A male patient 72 years old. The chart records prior skin cancer (patient or family) and no pesticide exposure. A clinical photograph showing a skin lesion. The patient was assessed as Fitzpatrick III — 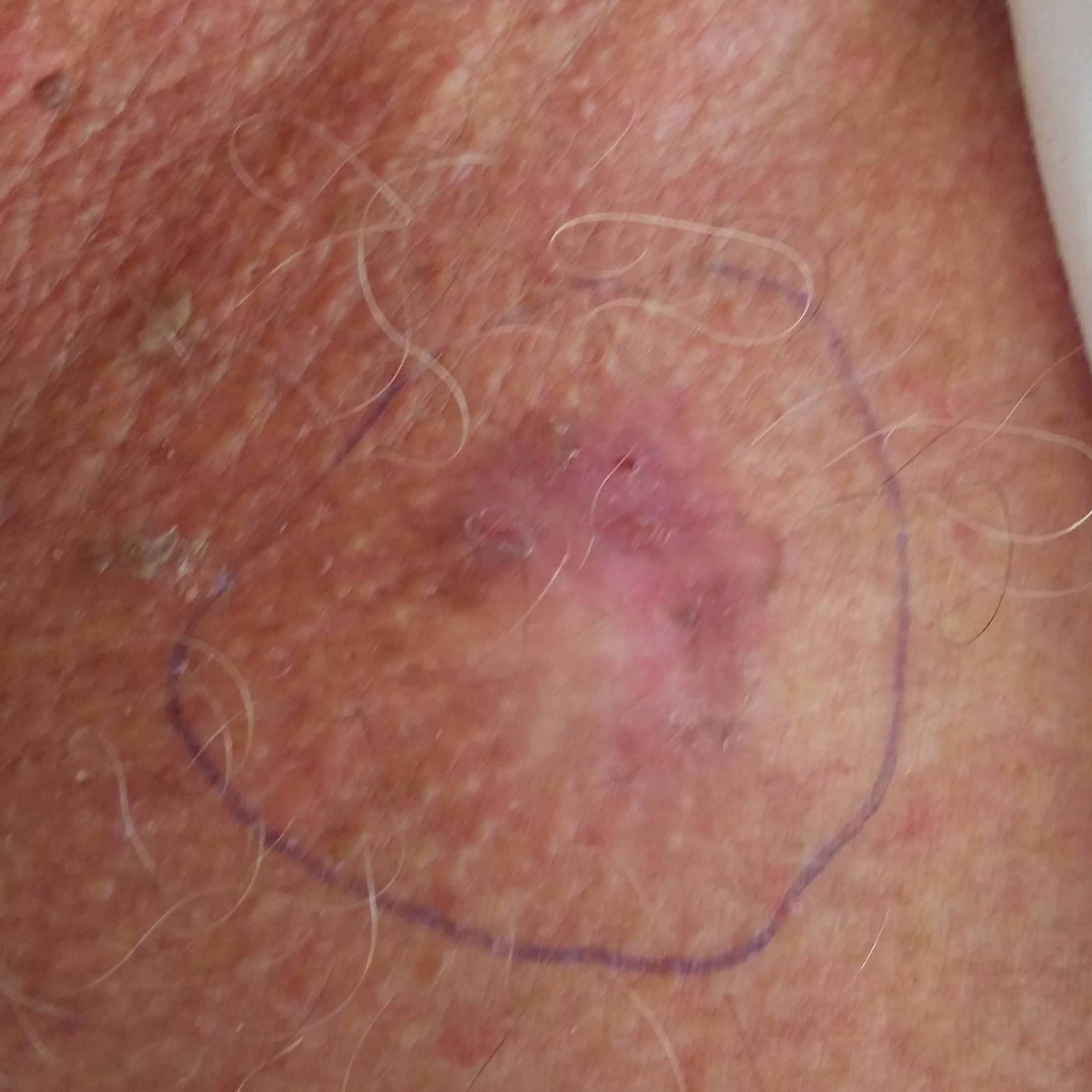Findings:
* region · the chest
* lesion size · 20 × 18 mm
* patient-reported symptoms · itching, elevation, growth, bleeding
* diagnosis · basal cell carcinoma (biopsy-proven)